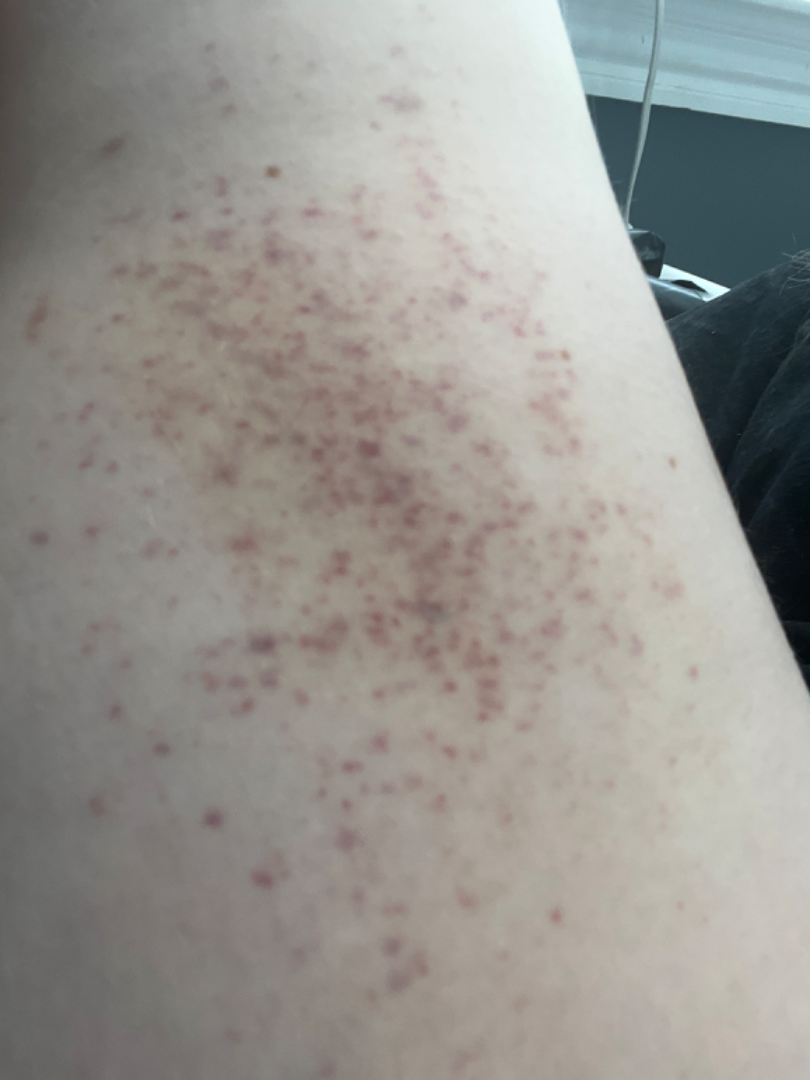location: leg
patient describes the issue as: a rash
photo taken: at an angle
patient-reported symptoms: itching
skin tone: Fitzpatrick I; non-clinician graders estimated MST 1–2
duration: less than one week
described texture: flat
dermatologist impression: the differential, in no particular order, includes Pigmented purpuric eruption, Eczema and Allergic Contact Dermatitis